A female patient, approximately 85 years of age or older; a dermoscopic image of a skin lesion:
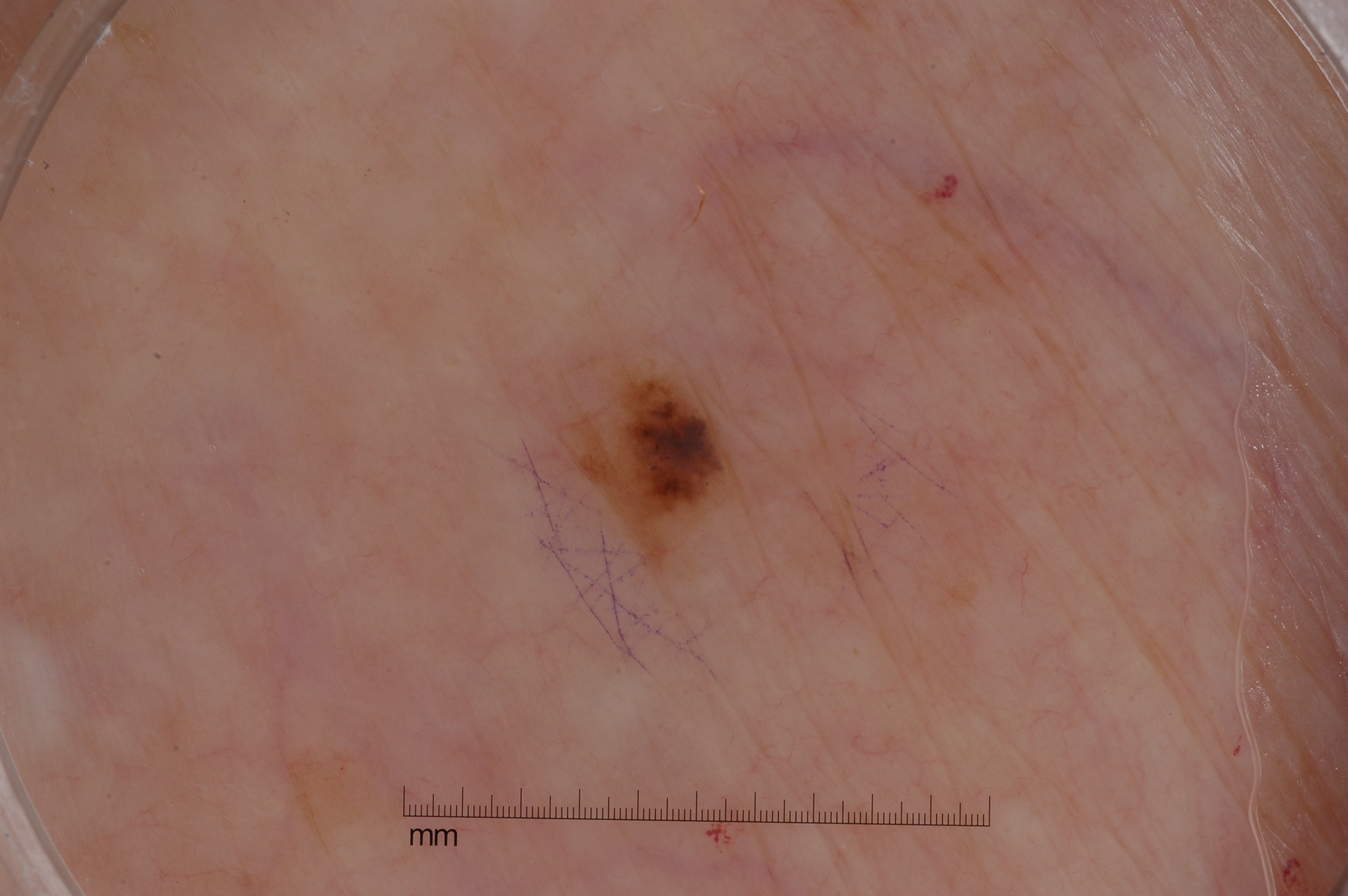Case summary:
* lesion size — ~2% of the field
* lesion bbox — [550, 362, 746, 575]
* absent dermoscopic features — streaks, milia-like cysts, pigment network, and negative network
* diagnosis — a melanocytic nevus